The lesion involves the head or neck, this is a close-up image:
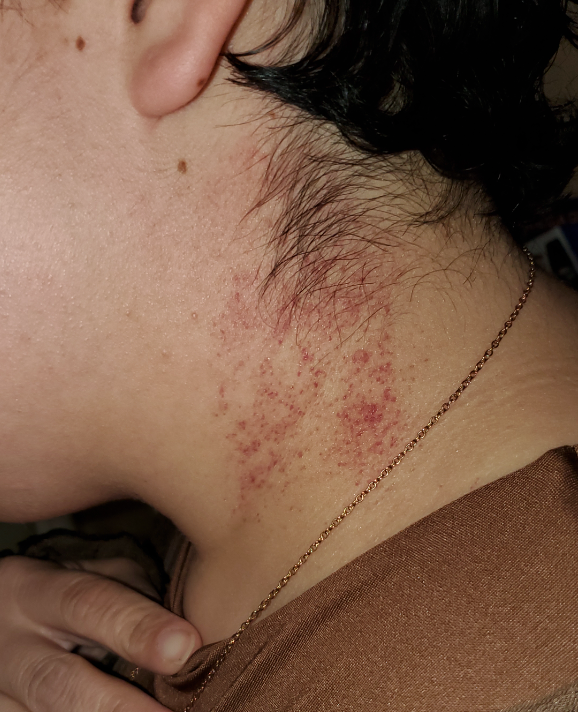  patient_category: a rash
  duration: about one day
  skin_tone:
    fitzpatrick: IV
    monk_skin_tone: 3
  symptoms: none reported
  texture: flat
  systemic_symptoms: fatigue
  differential:
    leading:
      - Purpura